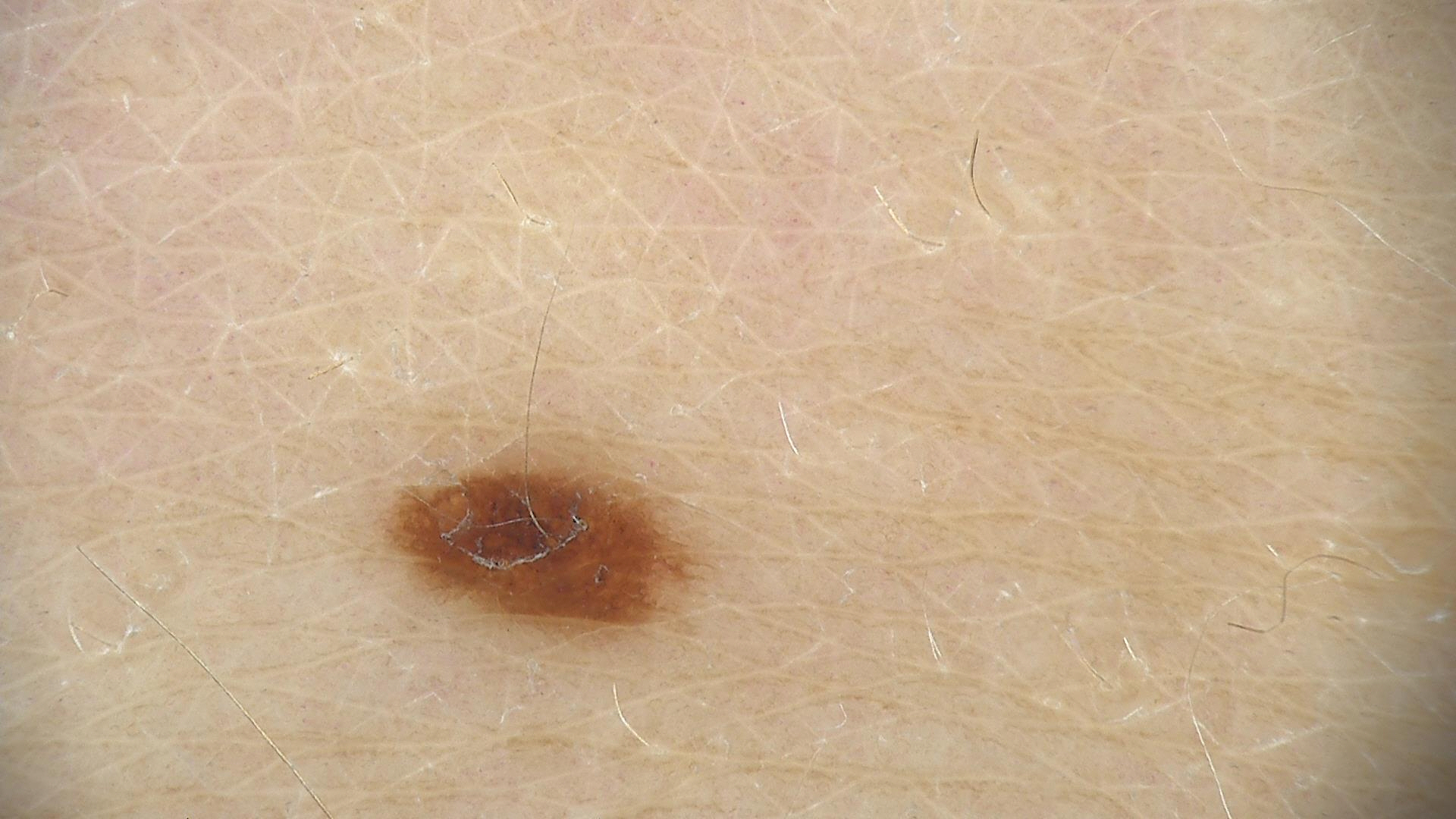image type=dermatoscopy; assessment=dysplastic junctional nevus (expert consensus).